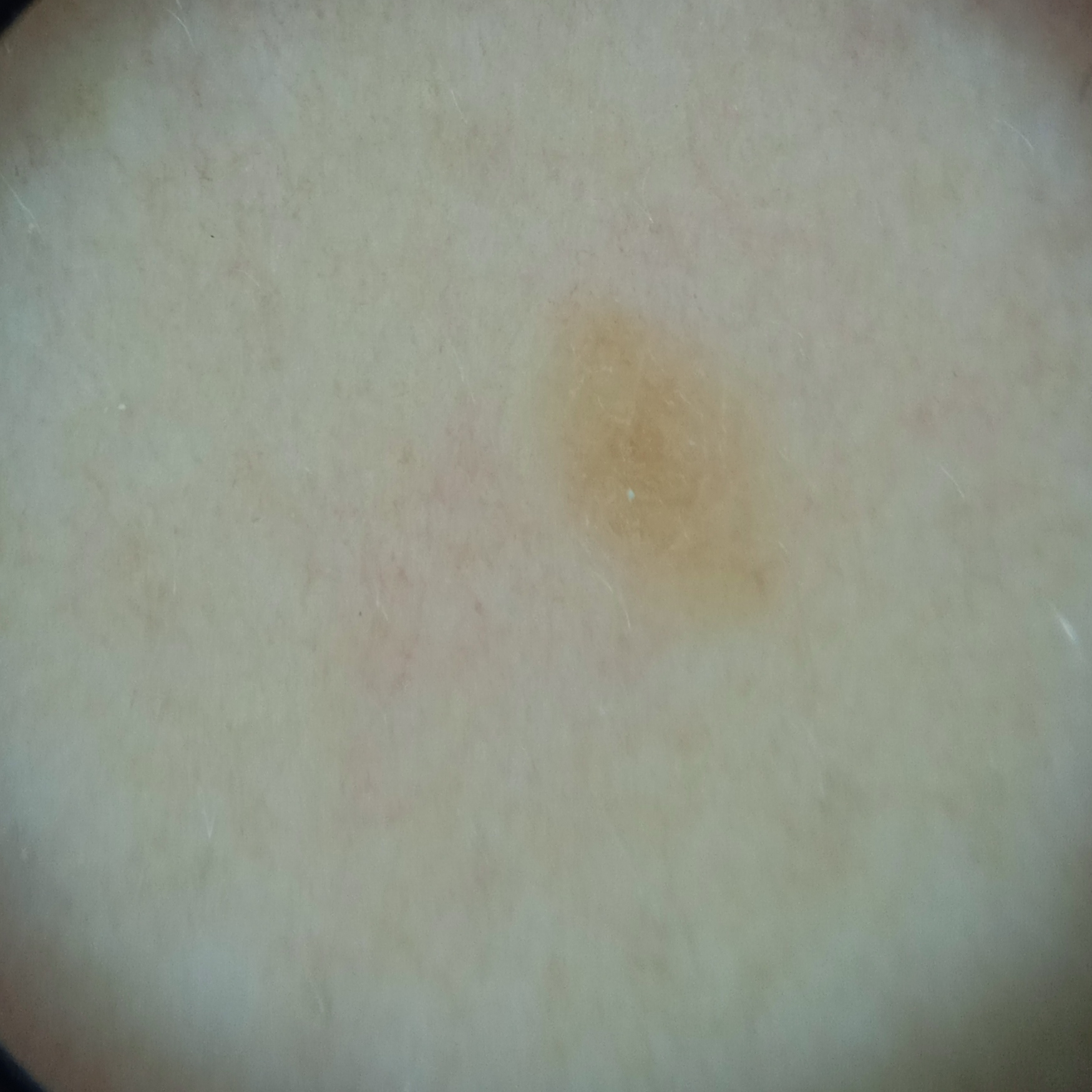Findings: A skin lesion imaged with a dermatoscope. A female subject 48 years of age. Imaged for a research study, with no referral diagnosis recorded. The lesion is on the back. The lesion measures approximately 3.8 mm. Assessment: The consensus diagnosis for this lesion was a seborrheic keratosis.